This image was taken at an angle. The affected area is the arm and front of the torso. The subject is 30–39, male.
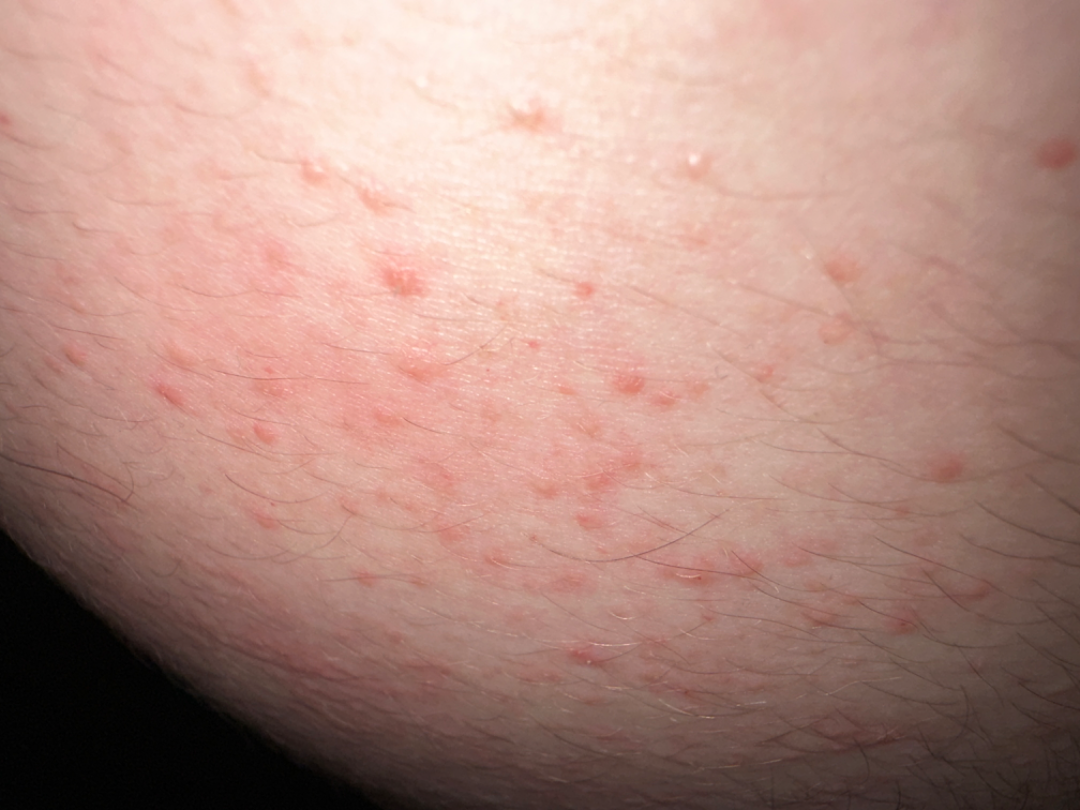assessment: not assessable
onset: one to four weeks
lesion symptoms: itching, bothersome appearance, pain, burning and enlargement
skin tone: FST II; lay reviewers estimated MST 2
self-categorized as: a rash
texture: raised or bumpy